The patient reported no systemic symptoms · a close-up photograph · the patient is a female aged 50–59 · reported lesion symptoms include bleeding:
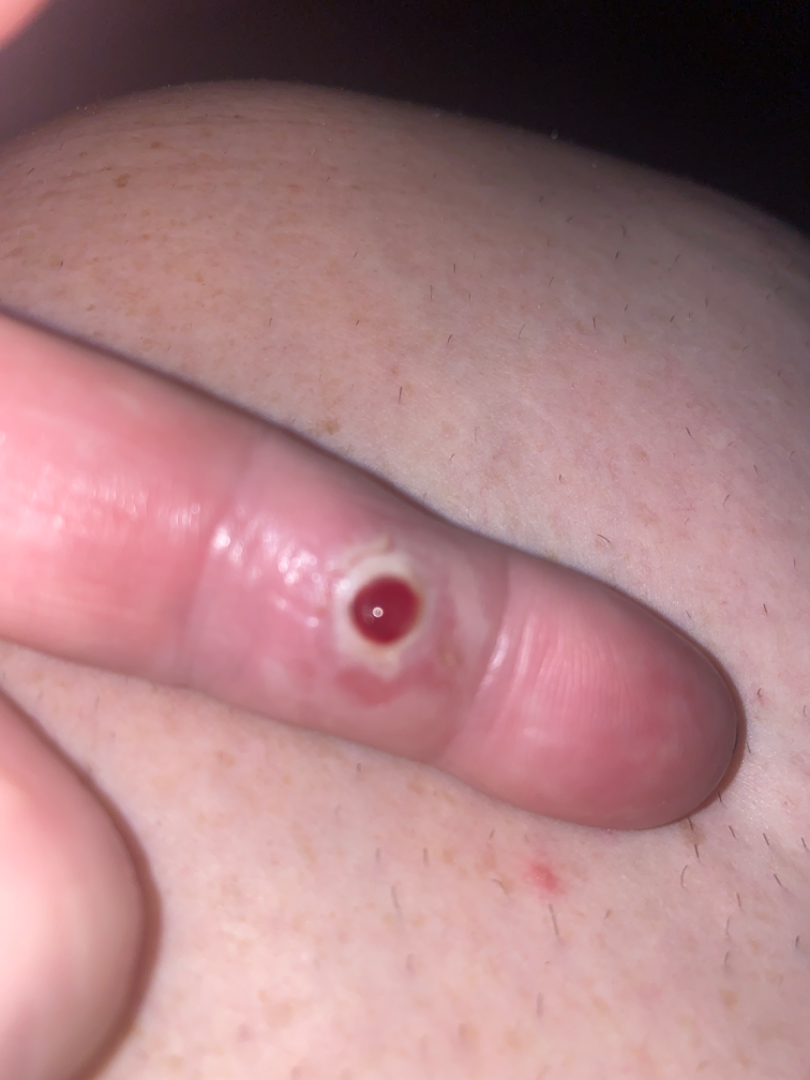assessment — most likely Pyogenic granuloma; the differential also includes Melanoma